Collected as part of a research study, without a referral diagnosis · a clinical close-up of a skin lesion · a moderate number of moles by the patient's own estimate · the patient reports a personal history of cancer and a personal history of skin cancer · the patient says their skin reddens with sun exposure:
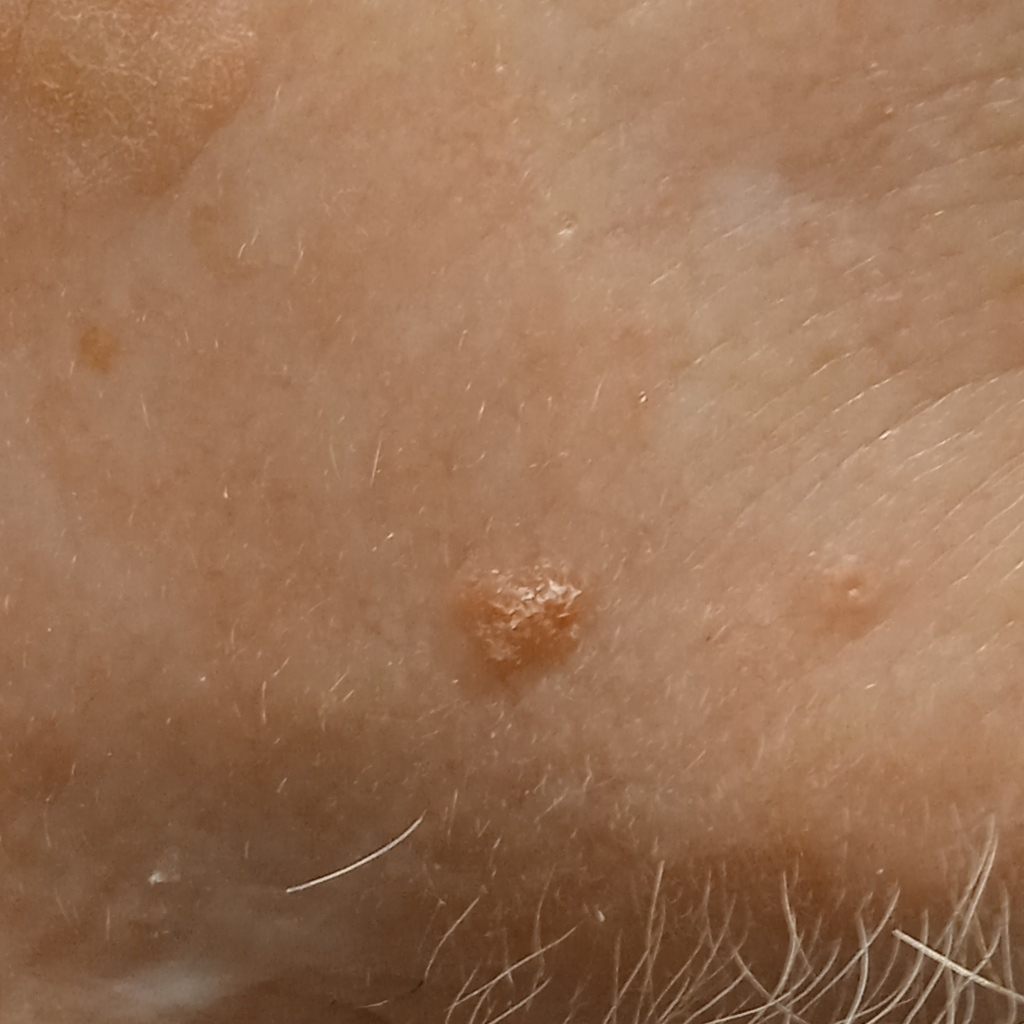The lesion is located on the face.
Measuring roughly 4.3 mm.
The diagnostic impression was an actinic keratosis.